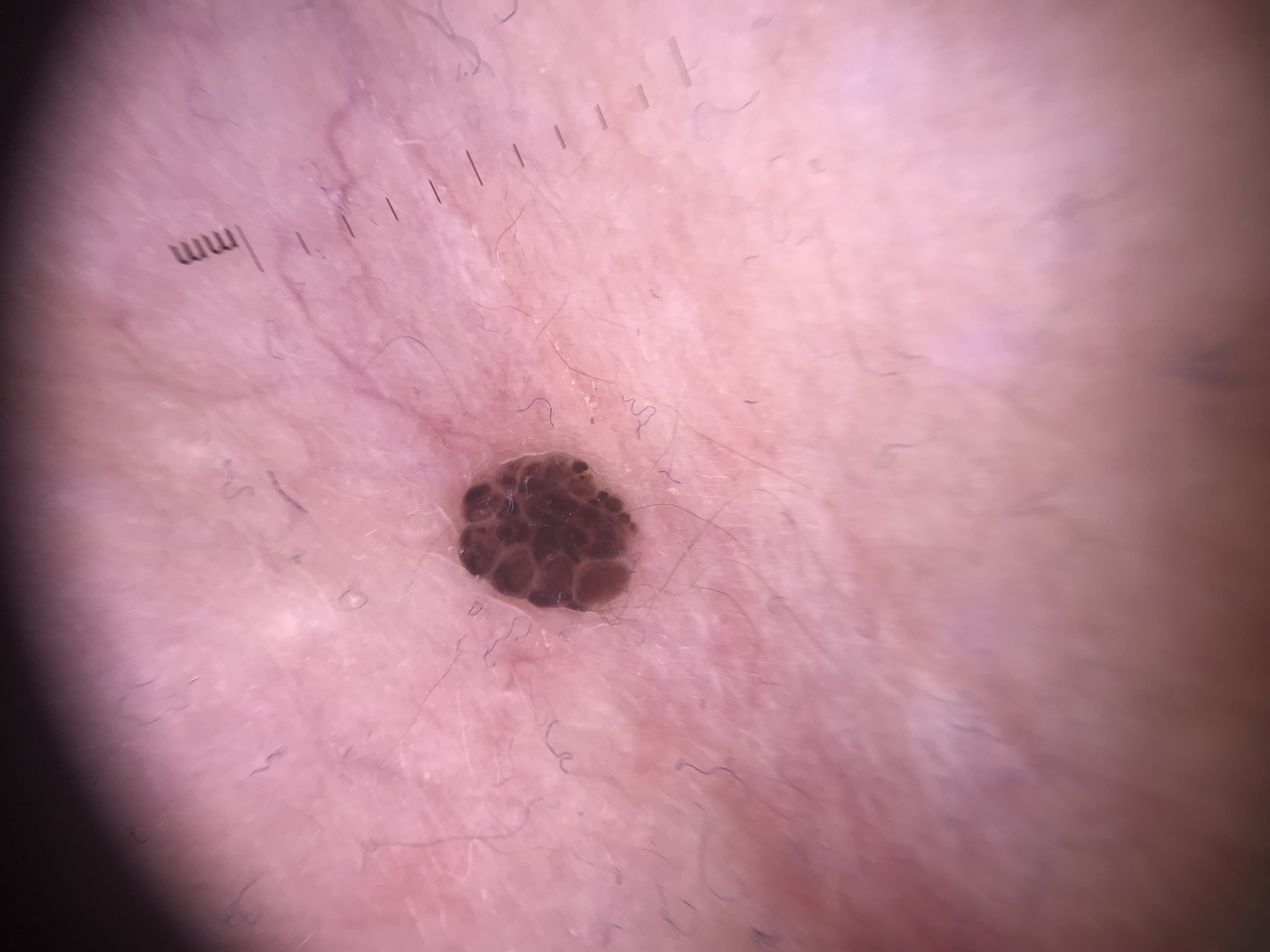imaging — dermatoscopy
subtype — banal
label — compound nevus (expert consensus)